The lesion is described as rough or flaky; reported duration is more than one year; the lesion is associated with itching; the contributor is male; the back of the torso is involved; this image was taken at an angle; the patient described the issue as a rash — 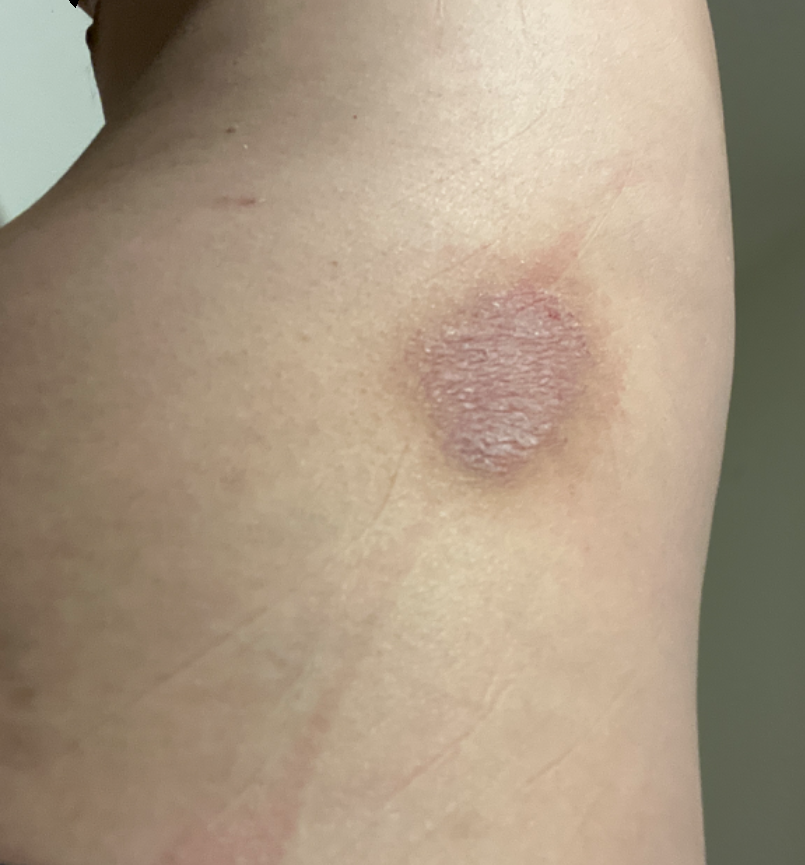Q: Could the case be diagnosed?
A: could not be assessed